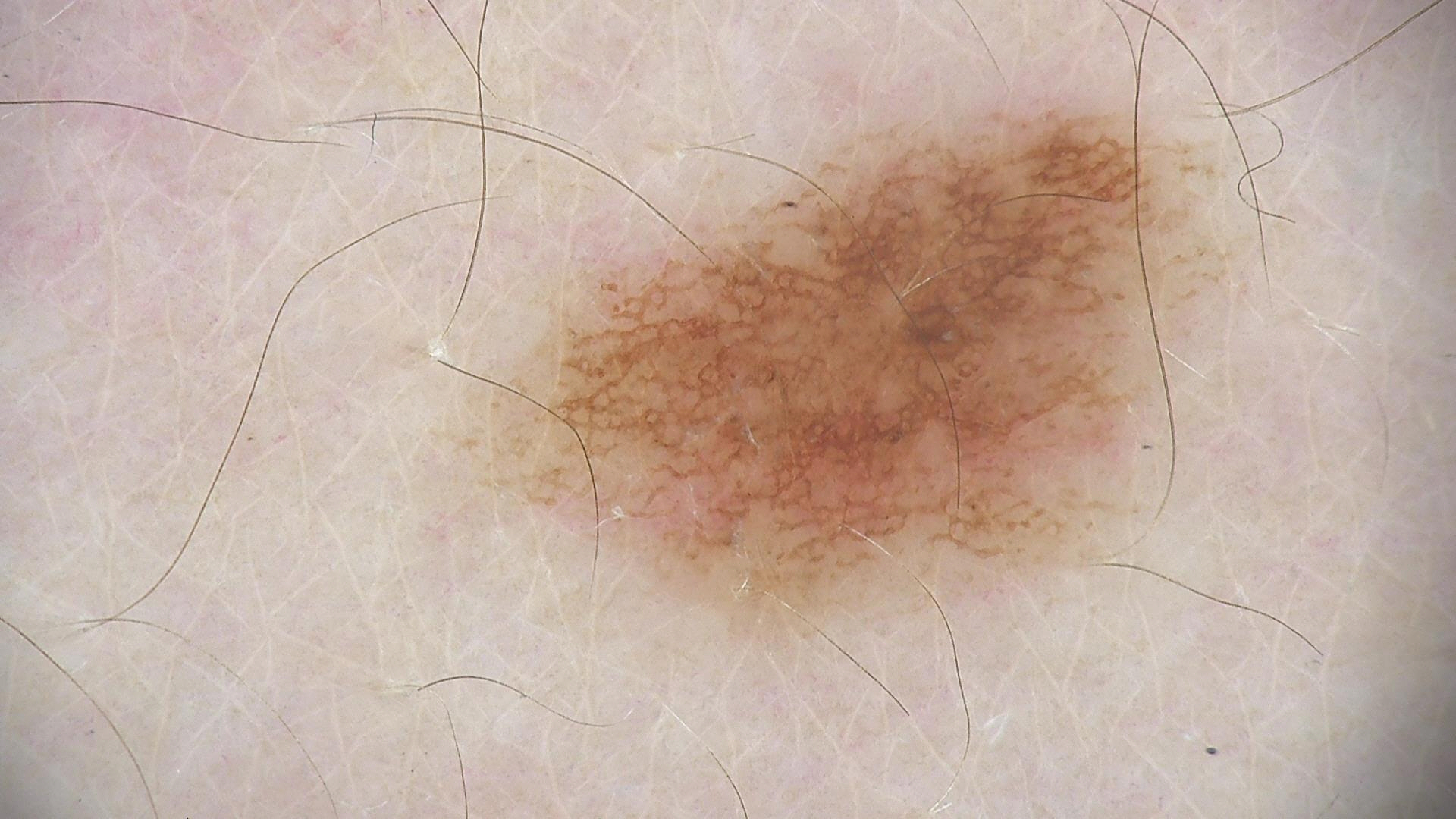A dermoscopy image of a single skin lesion. The diagnosis was a dysplastic junctional nevus.